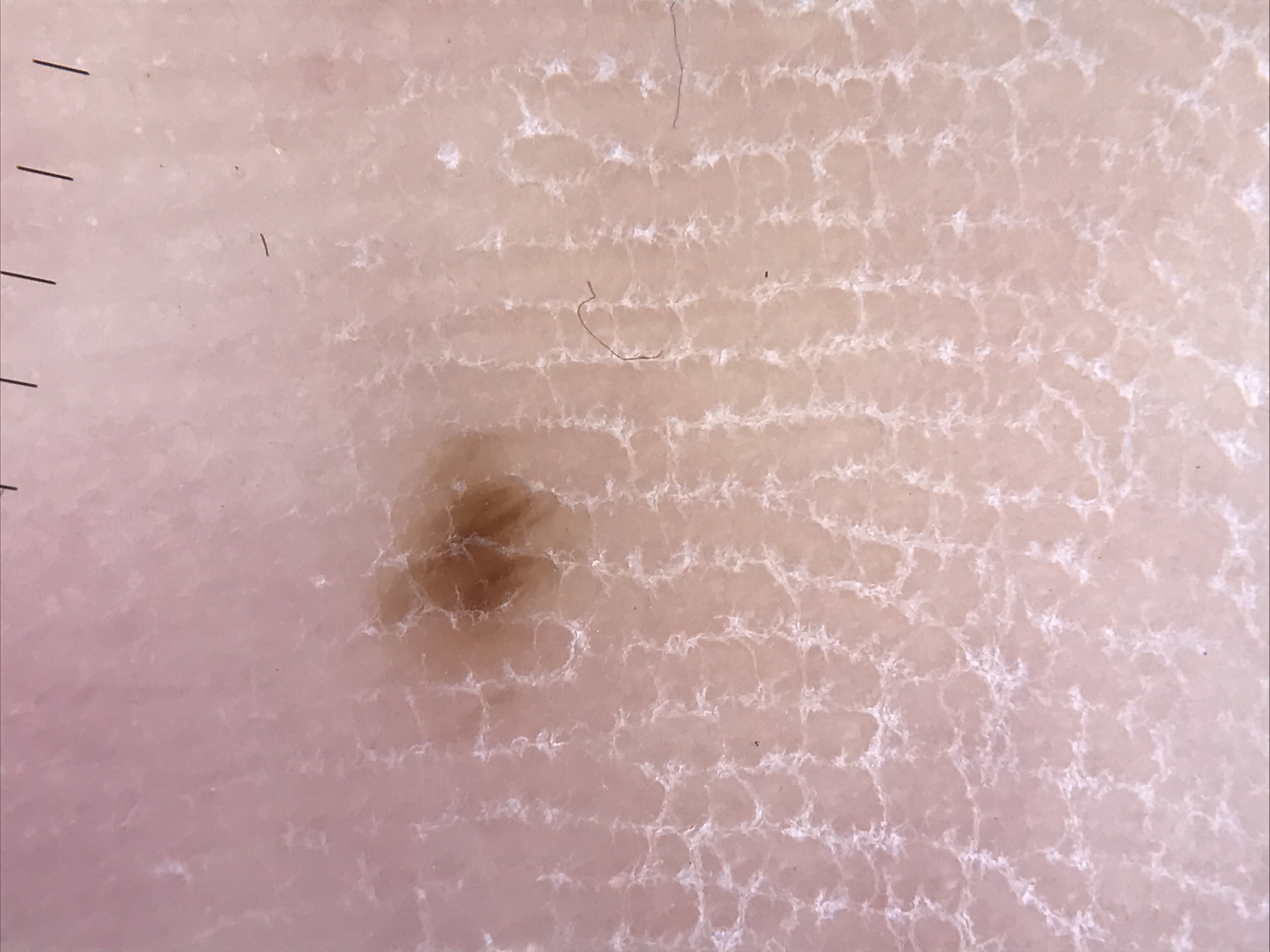Q: What kind of image is this?
A: dermatoscopy
Q: What kind of lesion is this?
A: banal
Q: What is this lesion?
A: acral junctional nevus (expert consensus)